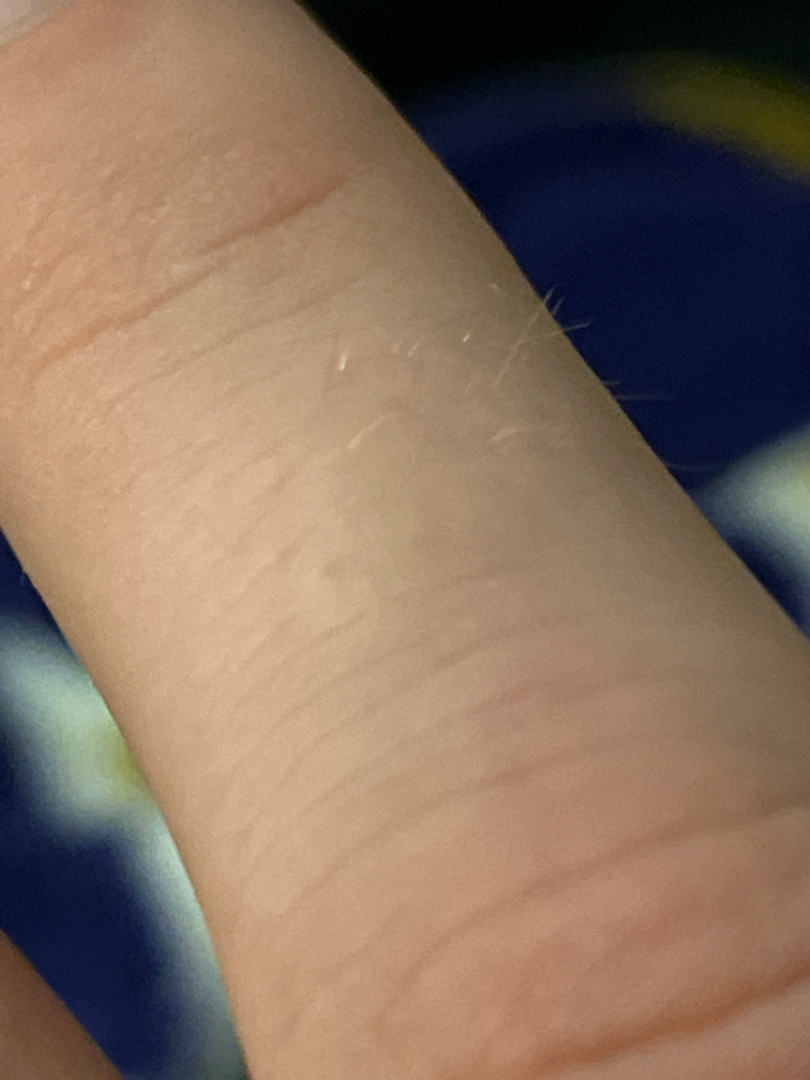The case was difficult to assess from the available photograph.
Texture is reported as raised or bumpy.
The photograph is a close-up of the affected area.
The lesion is associated with itching.